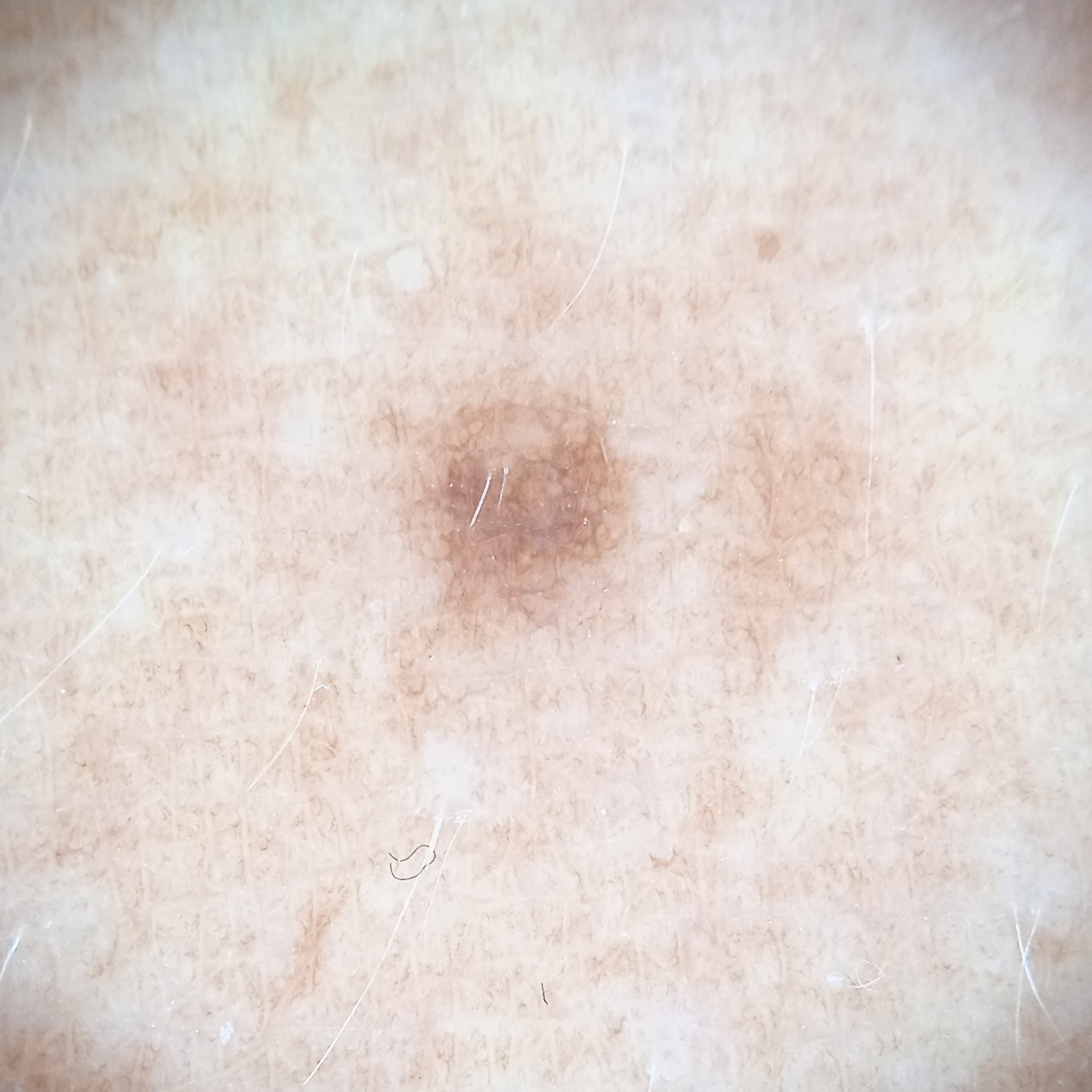nevus count = a moderate number of melanocytic nevi
subject = male, 54 years of age
relevant history = a personal history of cancer
location = an arm
lesion size = 2.9 mm
diagnosis = melanocytic nevus (dermatologist consensus)